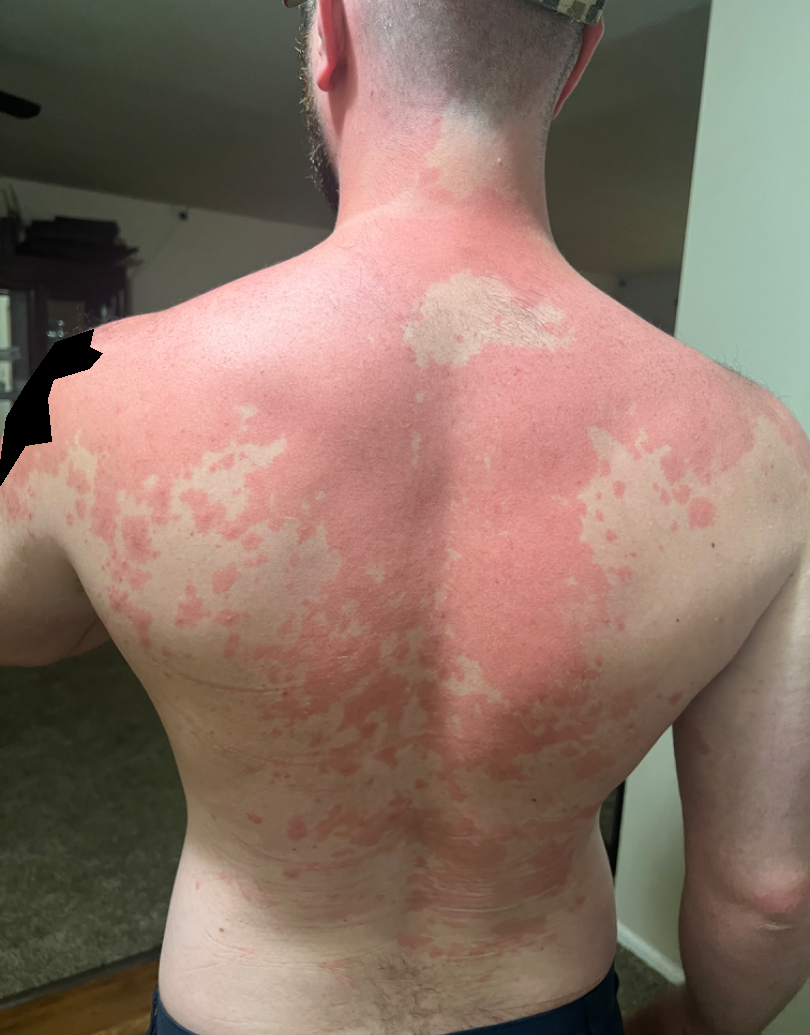{
  "differential": {
    "tied_lead": [
      "Drug Rash",
      "Urticaria",
      "Pityriasis rubra pilaris"
    ]
  }
}